A dermatoscopic image of a skin lesion.
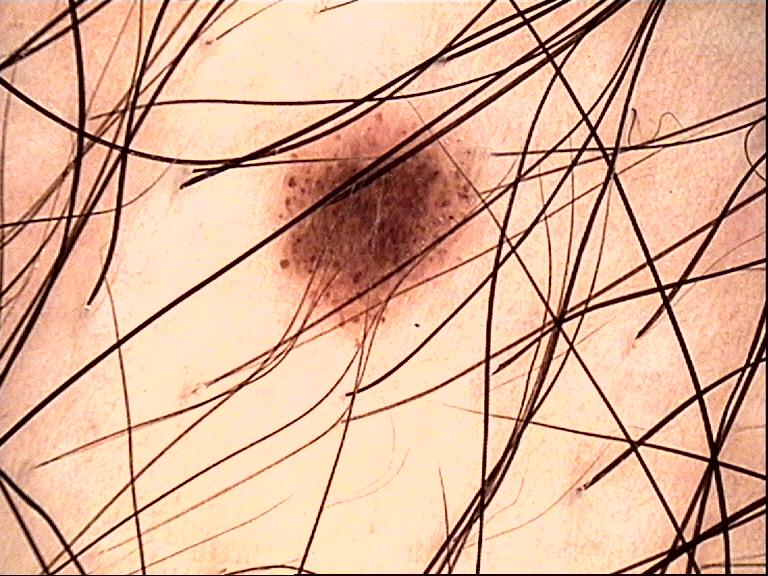Impression: Diagnosed as a benign lesion — a dysplastic junctional nevus.